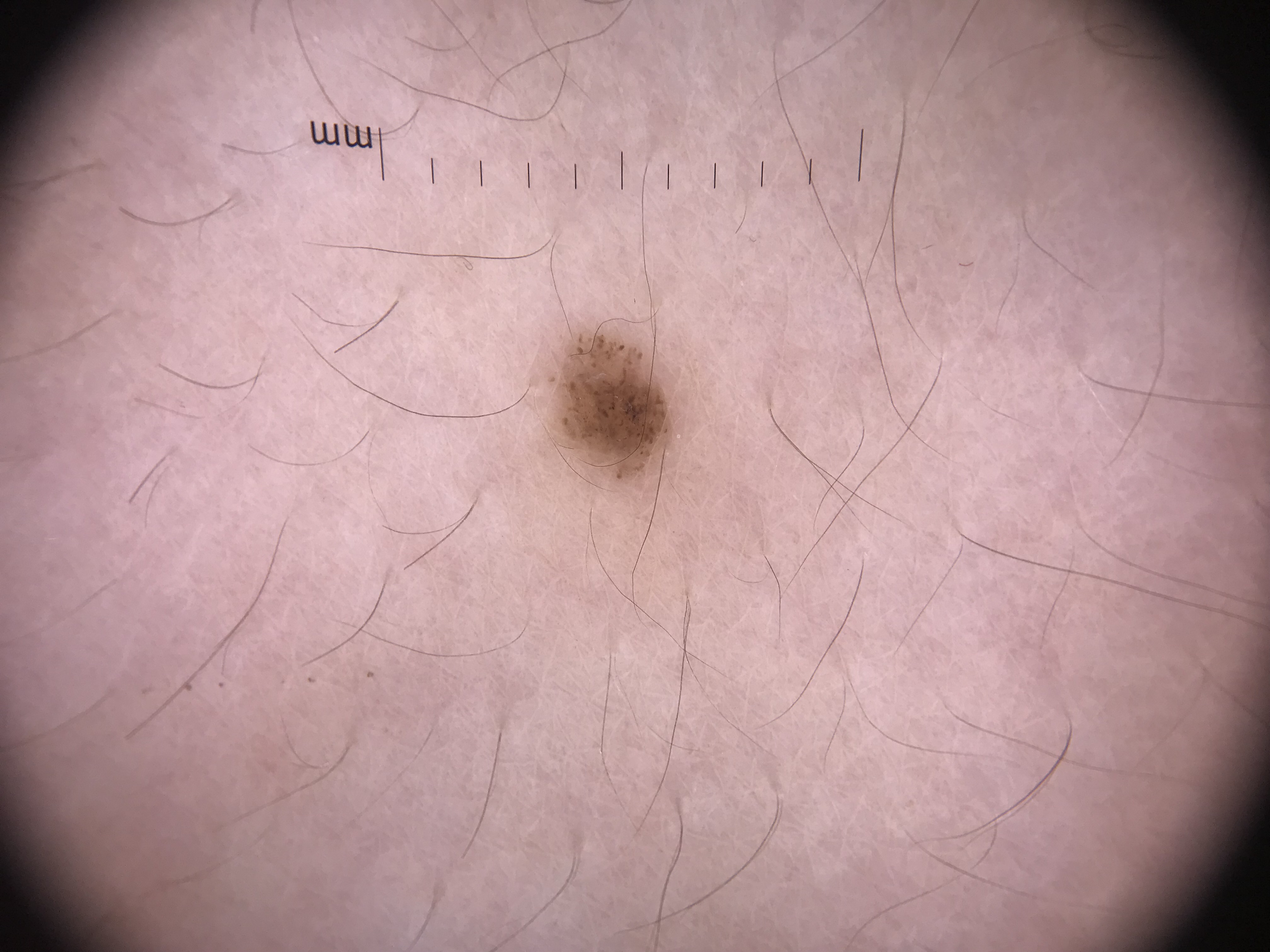<case>
  <image>dermatoscopy</image>
  <diagnosis>
    <name>dysplastic junctional nevus</name>
    <code>jd</code>
    <malignancy>benign</malignancy>
    <super_class>melanocytic</super_class>
    <confirmation>expert consensus</confirmation>
  </diagnosis>
</case>